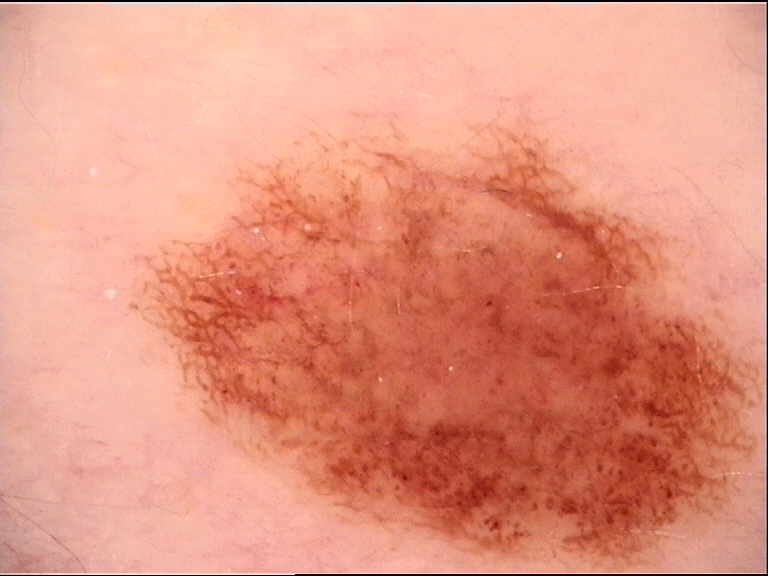A dermoscopic close-up of a skin lesion.
The diagnosis was a benign lesion — a dysplastic junctional nevus.